Dermoscopy of a skin lesion · a female subject aged 64.
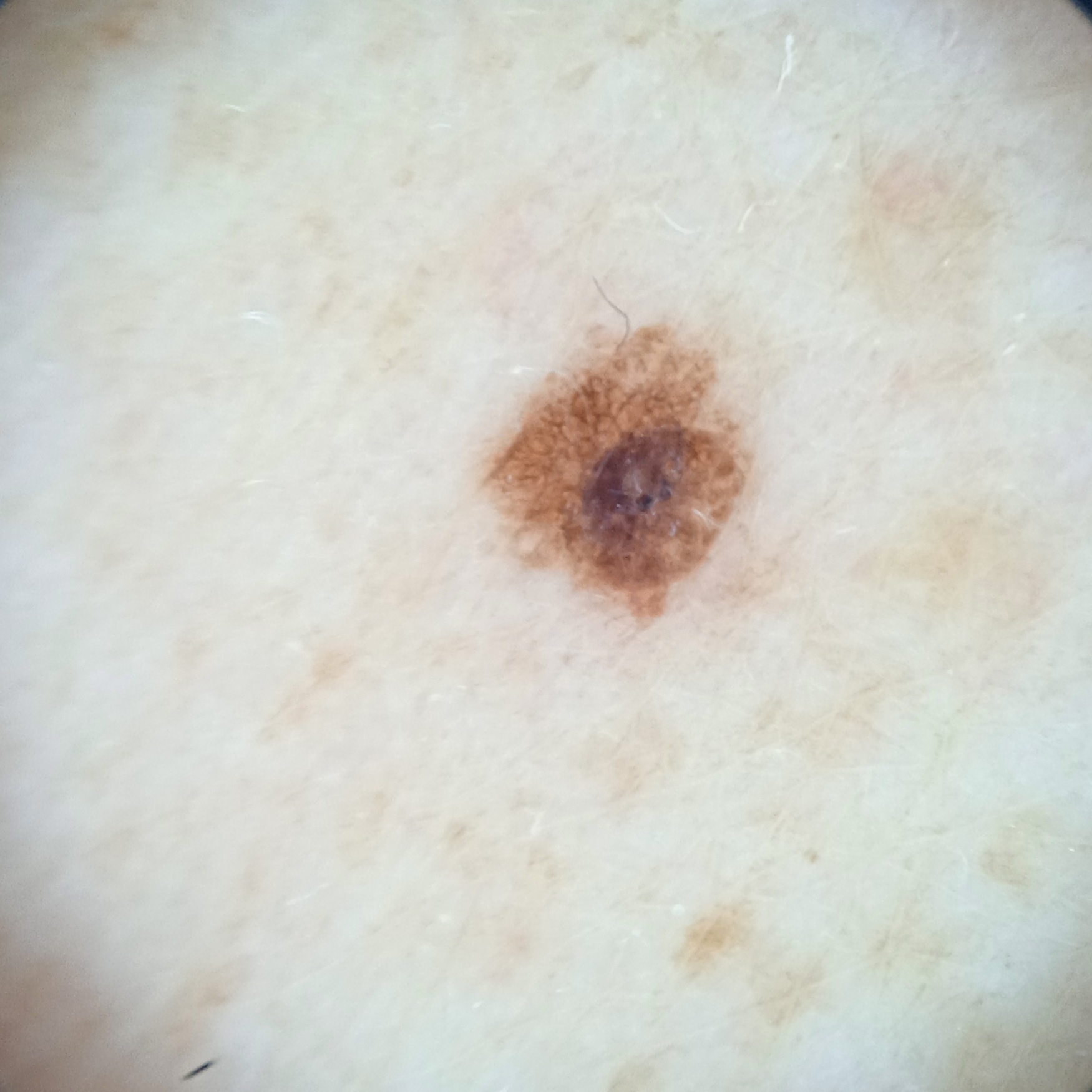diagnosis=seborrheic keratosis (biopsy-proven)